A dermoscopic close-up of a skin lesion:
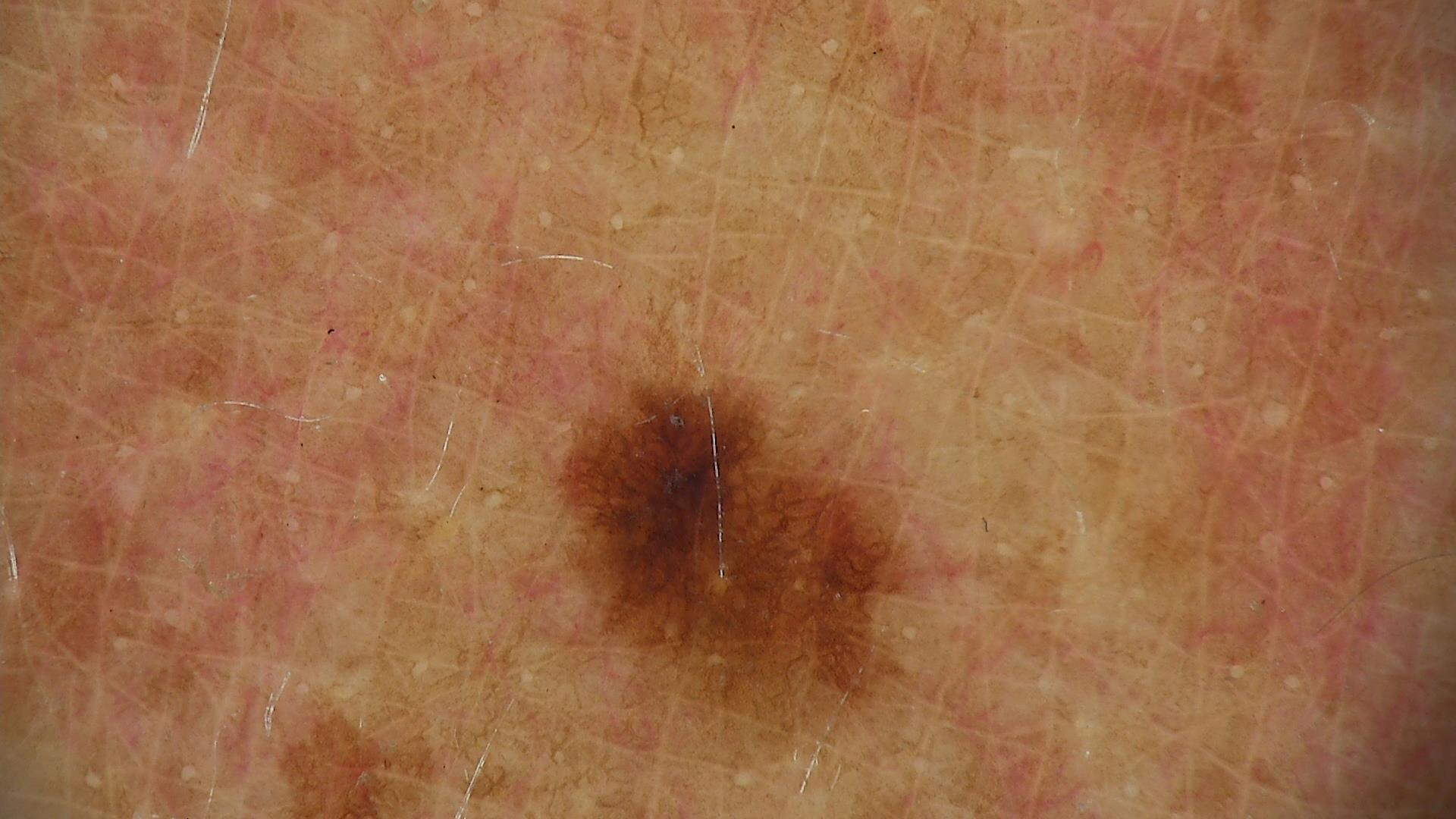<case>
<diagnosis>
<name>dysplastic junctional nevus</name>
<code>jd</code>
<malignancy>benign</malignancy>
<super_class>melanocytic</super_class>
<confirmation>expert consensus</confirmation>
</diagnosis>
</case>